This image was taken at an angle:
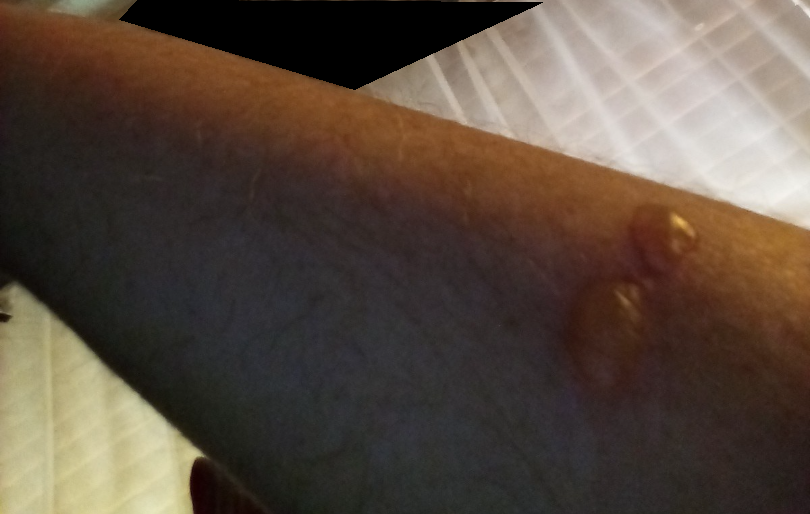clinical impression = most consistent with Bullous Pemphigoid.